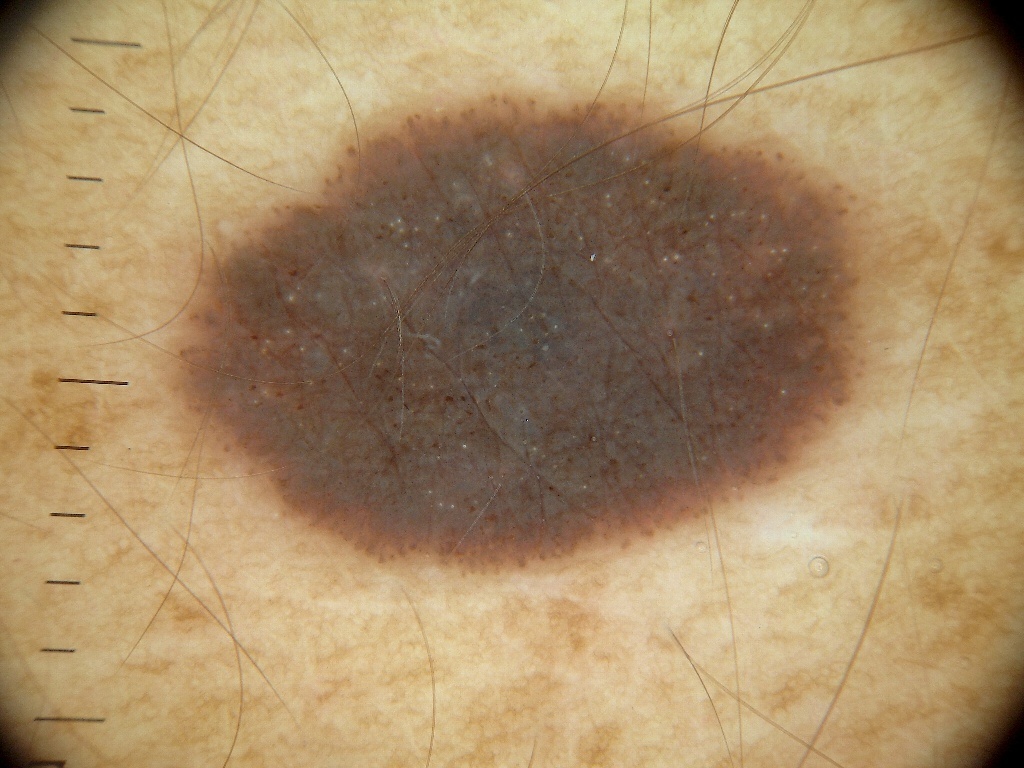– patient — female, in their 30s
– image — dermoscopy of a skin lesion
– lesion bbox — x1=167, y1=88, x2=869, y2=582
– features — streaks and milia-like cysts; absent: globules, negative network, and pigment network
– size — large
– diagnosis — a melanocytic nevus